A dermatoscopic image of a skin lesion.
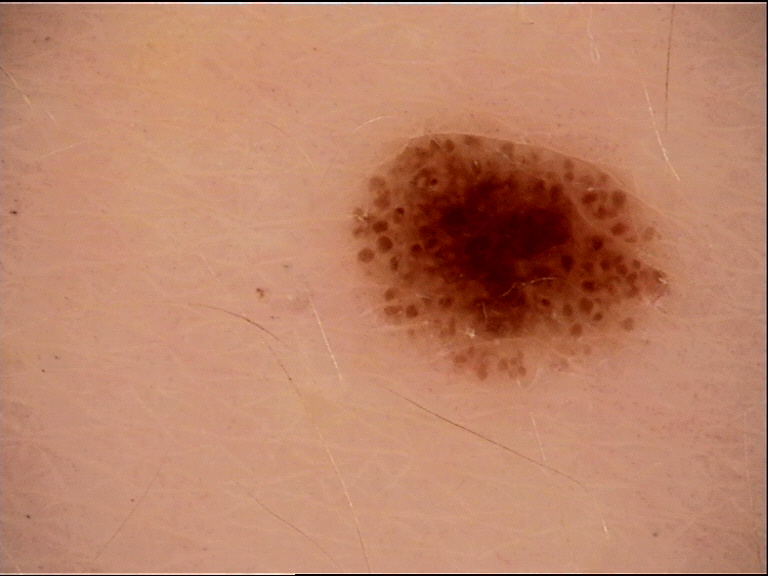The diagnostic label was a dysplastic junctional nevus.